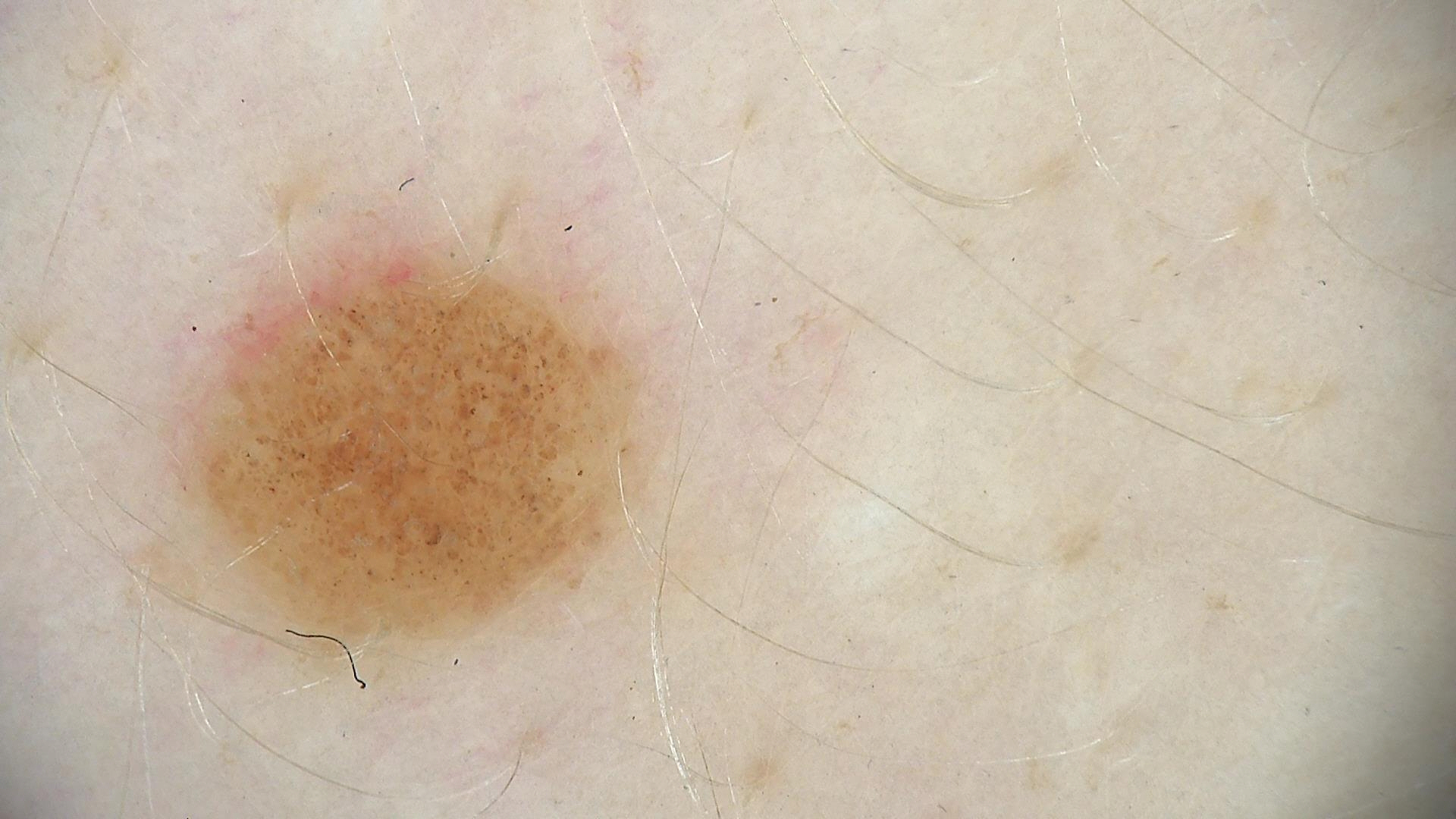image: dermatoscopy | diagnostic label: dysplastic junctional nevus (expert consensus).